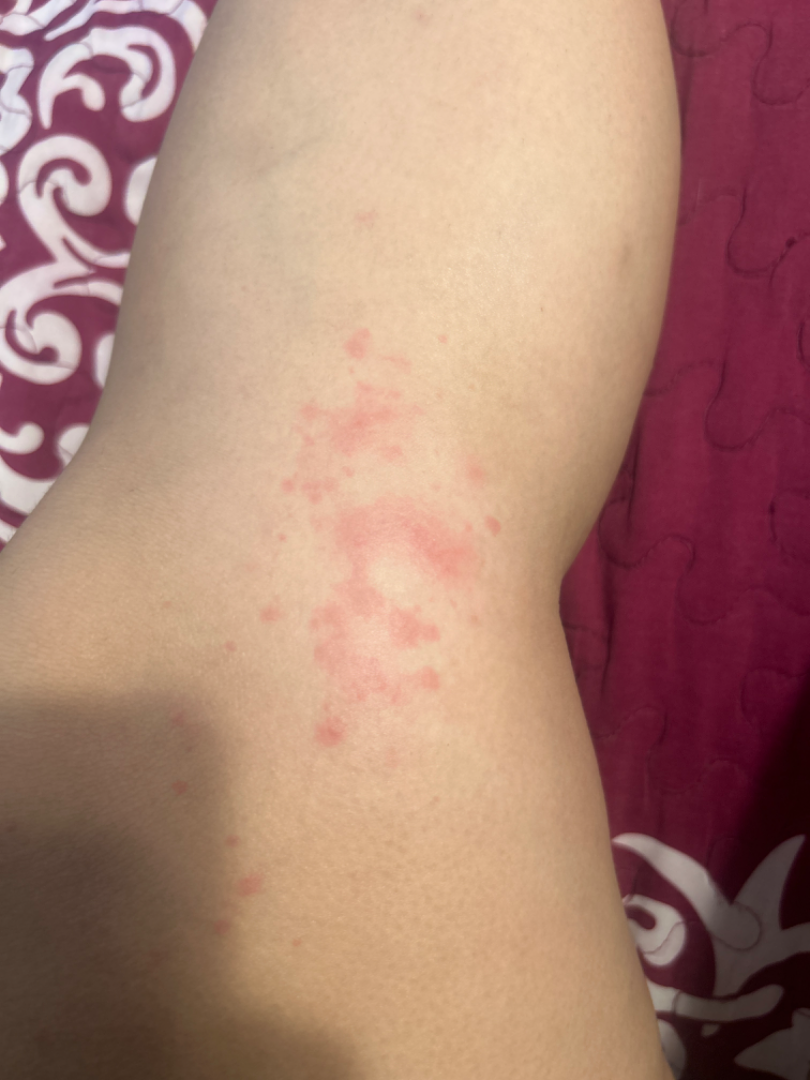Clinical context:
This is a close-up image. Self-categorized by the patient as skin that appeared healthy to them. Female contributor, age 18–29. Texture is reported as raised or bumpy. The lesion involves the back of the torso, front of the torso and leg. The contributor reports burning and itching. The contributor reports the condition has been present for less than one week.
Assessment:
Most likely Allergic Contact Dermatitis; a remote consideration is Eczema; less likely is Dermatitis herpetiformis; less probable is Insect Bite; a more distant consideration is Folliculitis.